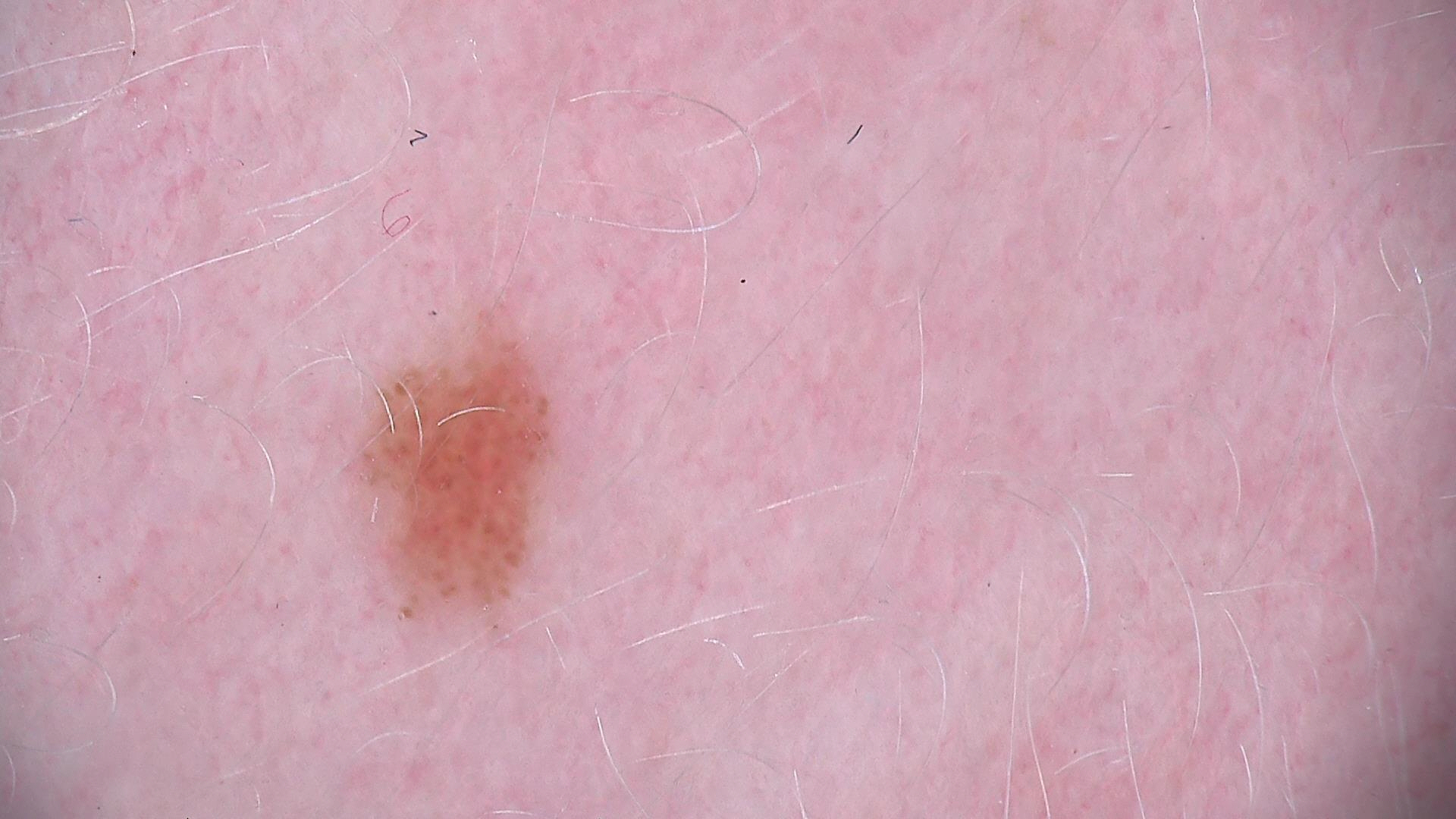diagnostic label — dysplastic junctional nevus (expert consensus)